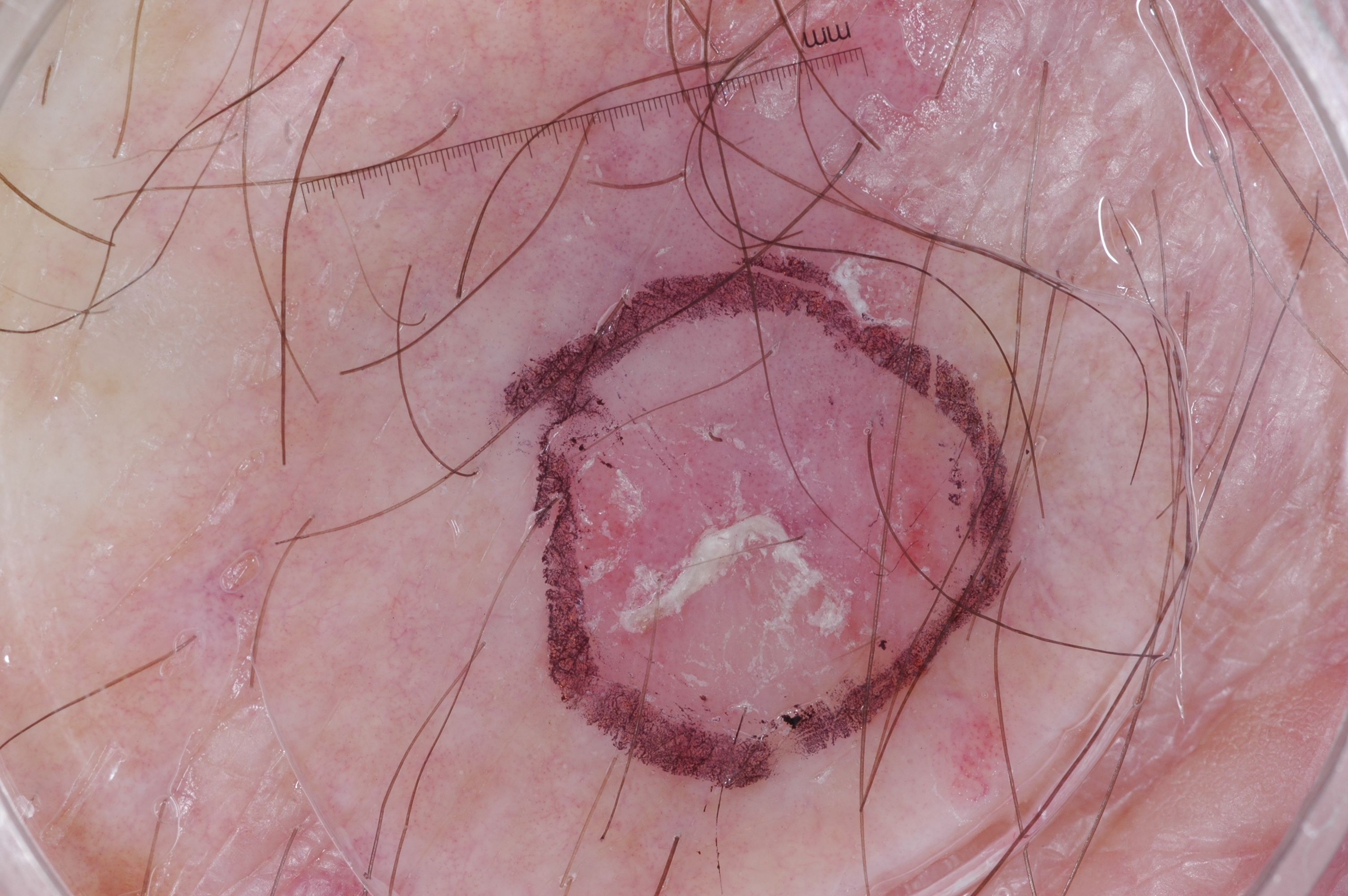Findings: The subject is a male approximately 65 years of age. A dermoscopy image of a single skin lesion. The lesion's extent is x1=556, y1=279, x2=996, y2=761. A mid-sized lesion within the field. The dermoscopic pattern shows no pigment network, streaks, negative network, or milia-like cysts. Conclusion: The diagnostic assessment was a seborrheic keratosis, a benign skin lesion.